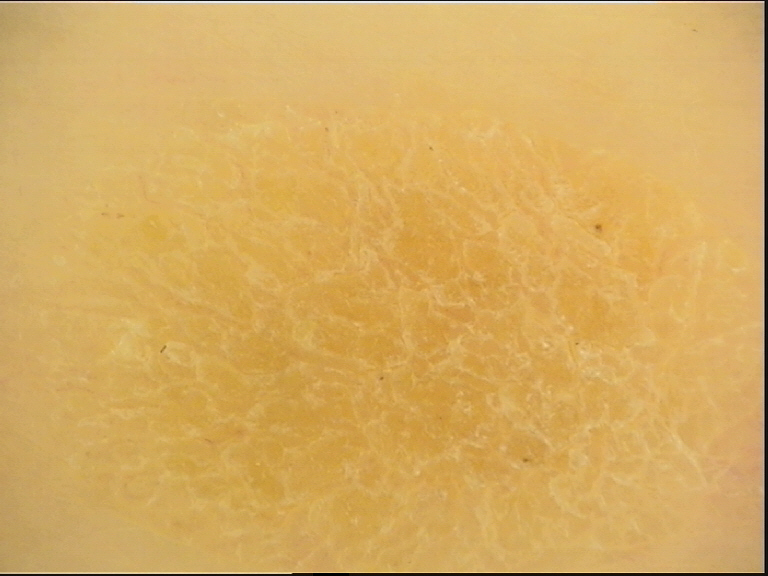label: seborrheic keratosis (expert consensus)